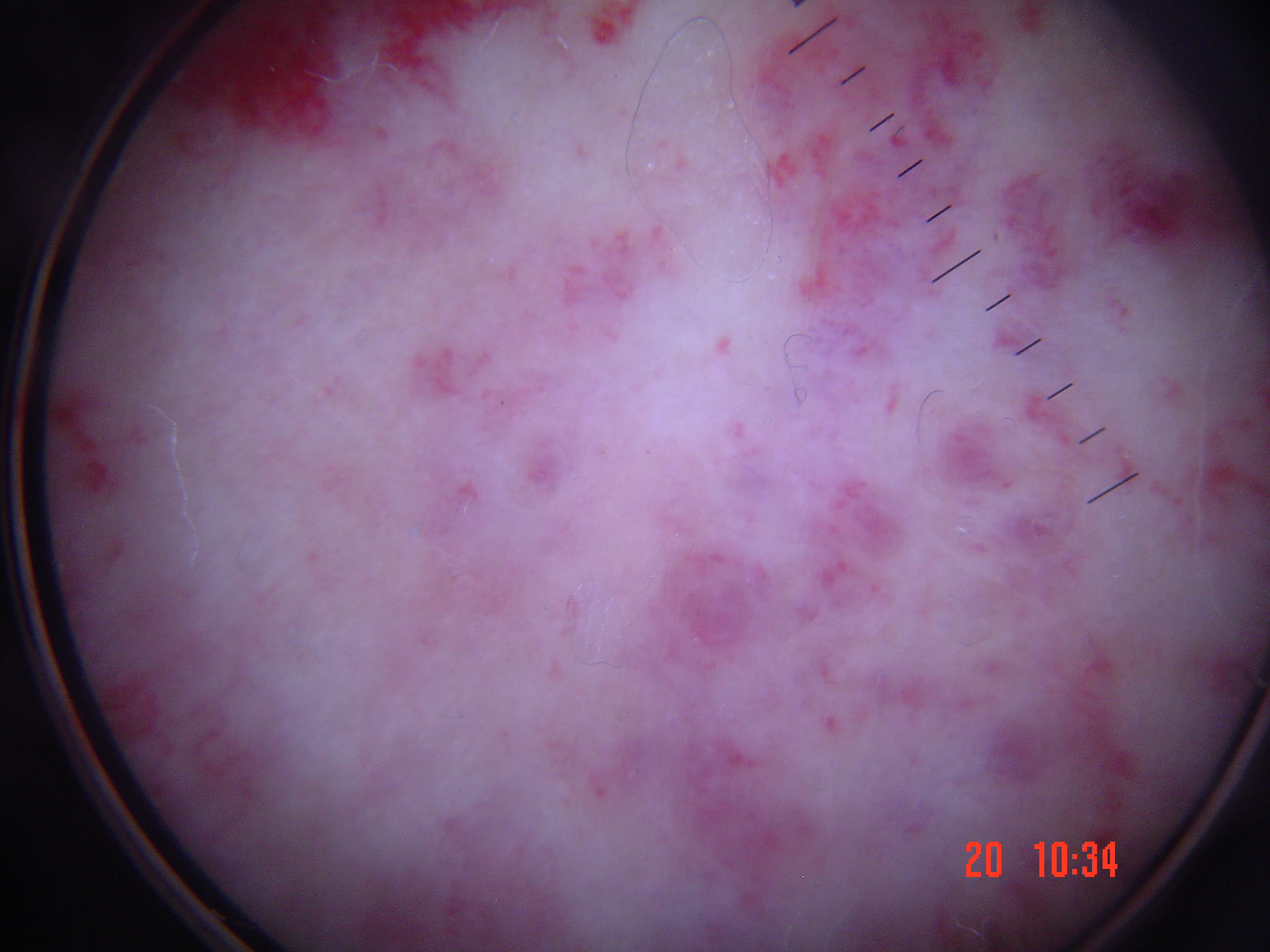Conclusion: Labeled as a vascular lesion — a hemangioma.